A clinical photo of a skin lesion taken with a smartphone; a female patient in their late 40s; the chart notes pesticide exposure and prior skin cancer (patient or family) — 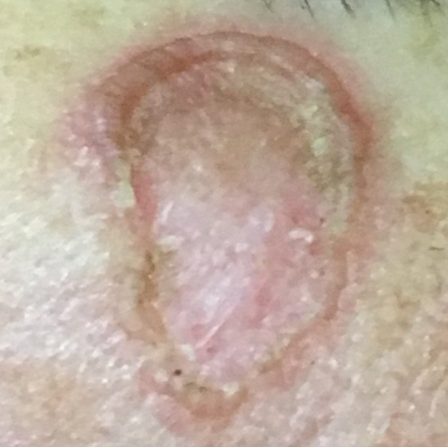The lesion is on the face. Measuring about 13 × 9 mm. The patient describes that the lesion has grown, hurts, itches, is elevated, and has changed. On biopsy, the diagnosis was a lesion of indeterminate malignant potential — an actinic keratosis.